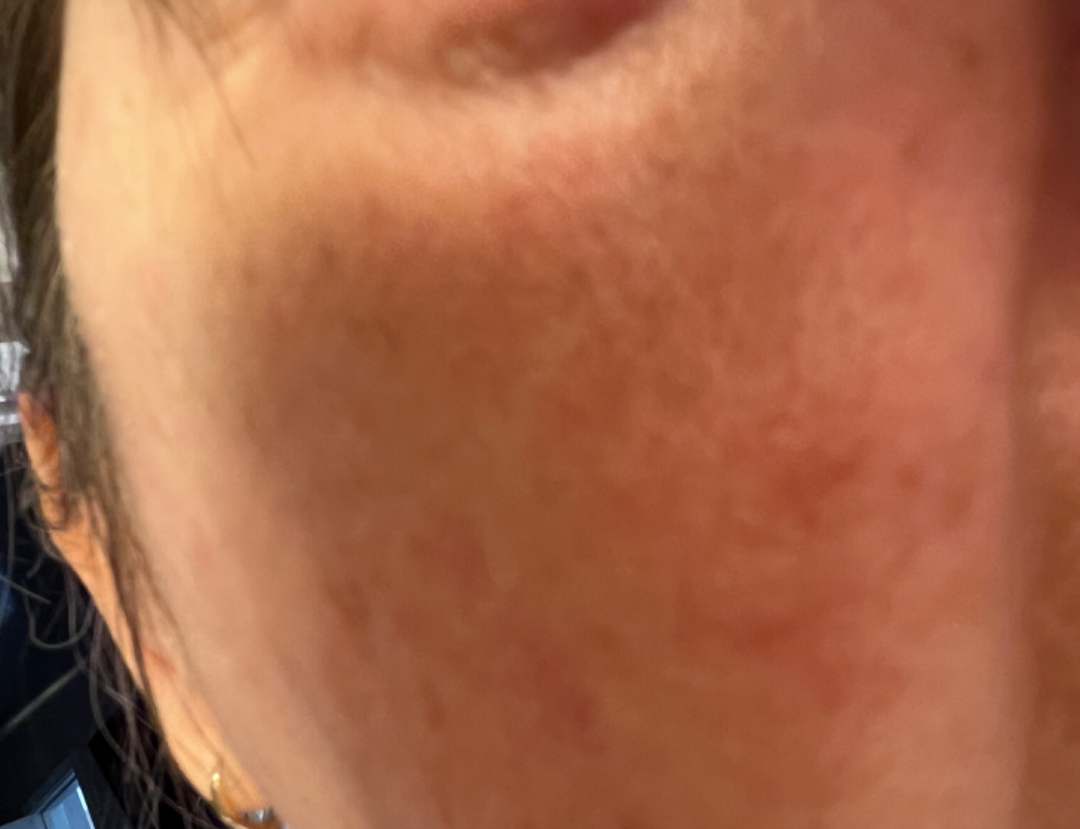assessment = not assessable
image framing = close-up
location = head or neck